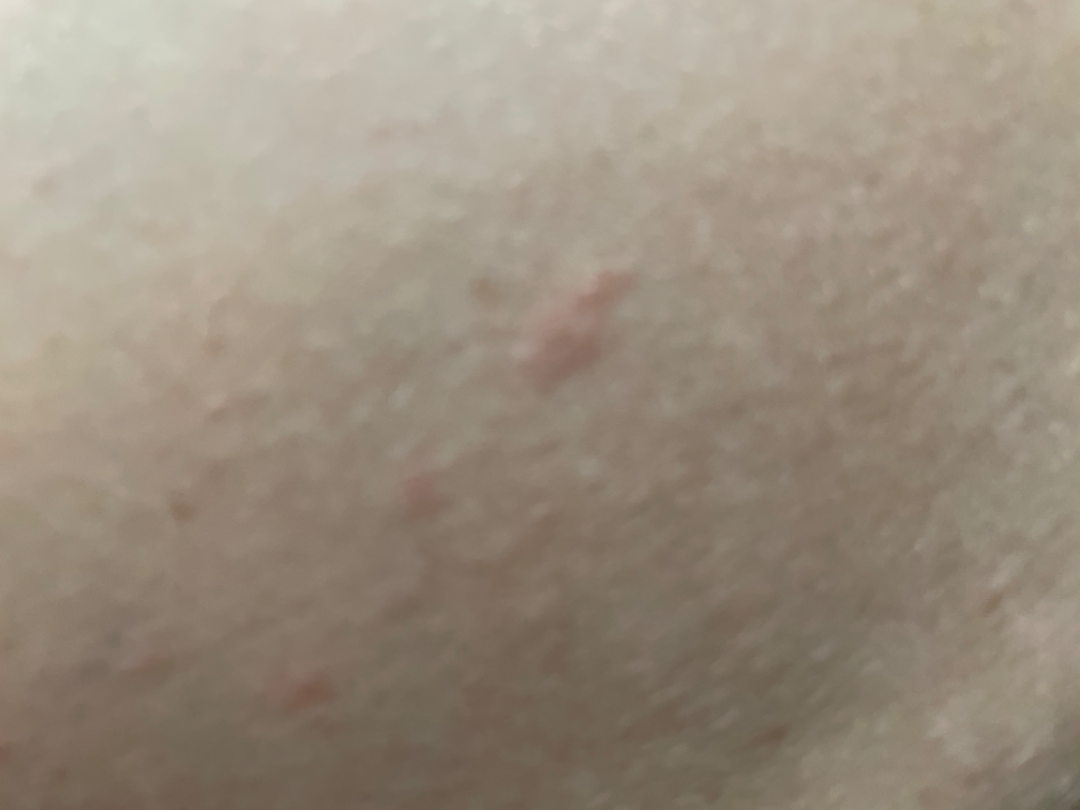assessment = could not be assessed.